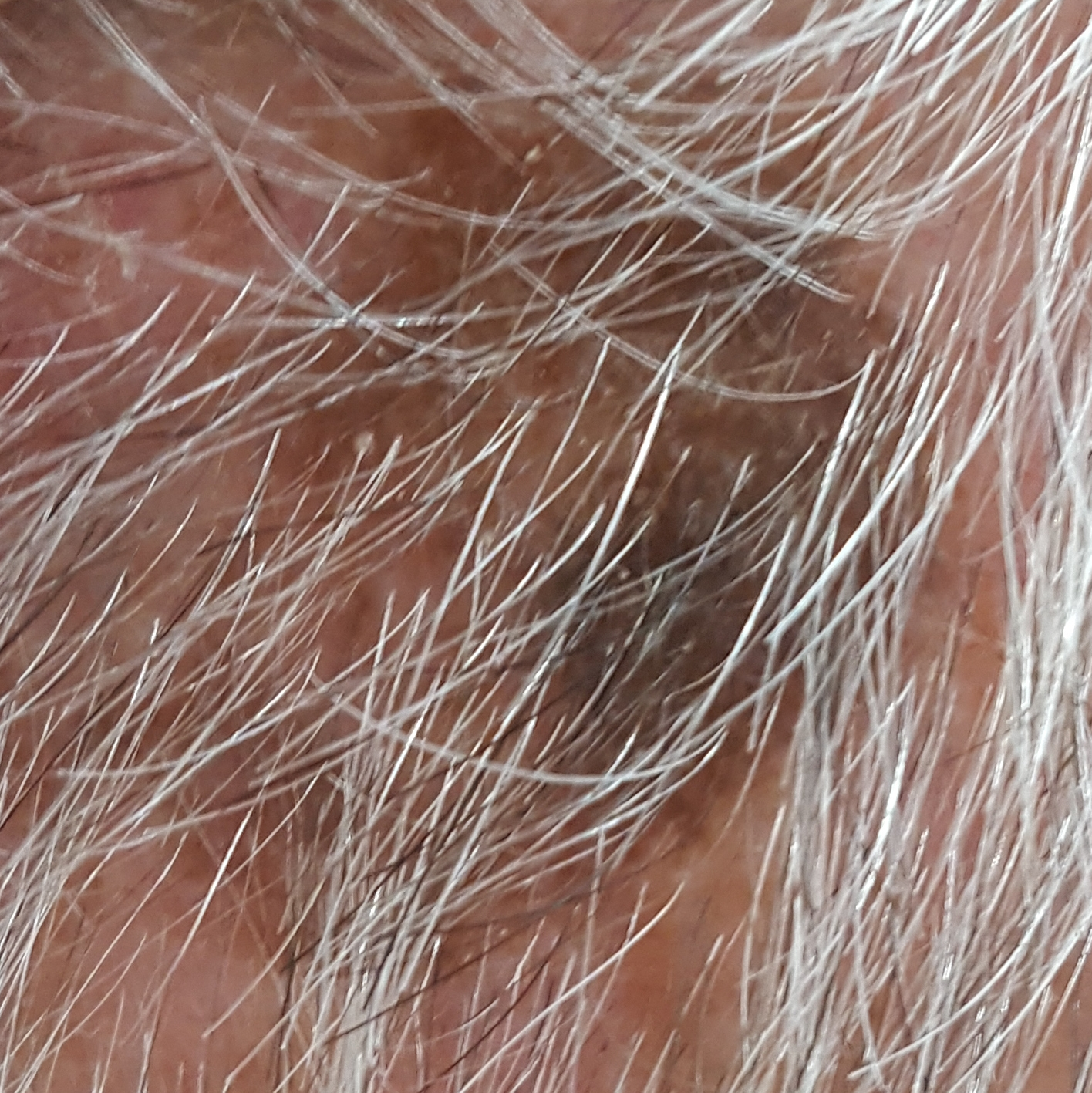  patient:
    age: 68
  image: smartphone clinical photo
  diagnosis:
    name: seborrheic keratosis
    code: SEK
    malignancy: benign
    confirmation: clinical consensus